The photograph was taken at an angle. The contributor is female. The front of the torso and arm are involved:
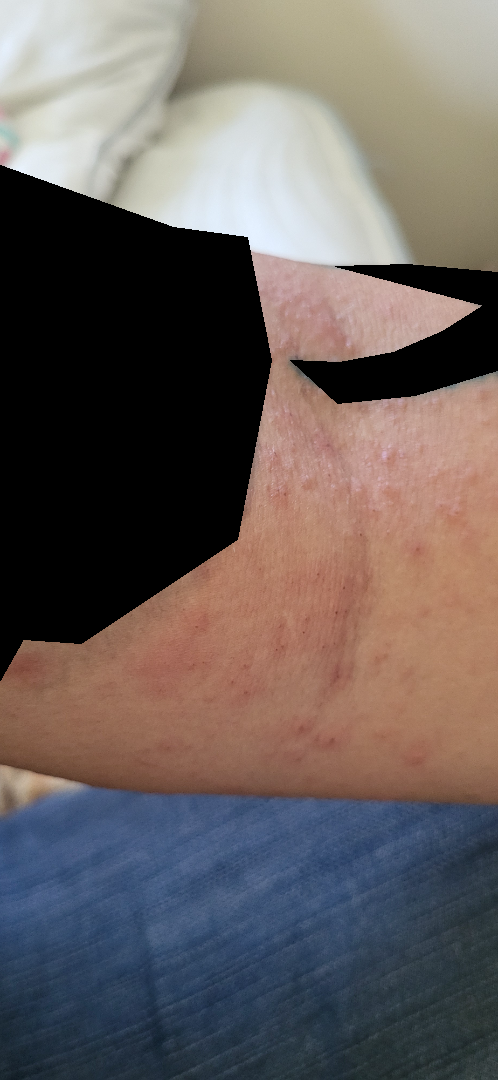On teledermatology review, most consistent with Lichen Simplex Chronicus; less probable is Eczema; lower on the differential is Psoriasis.